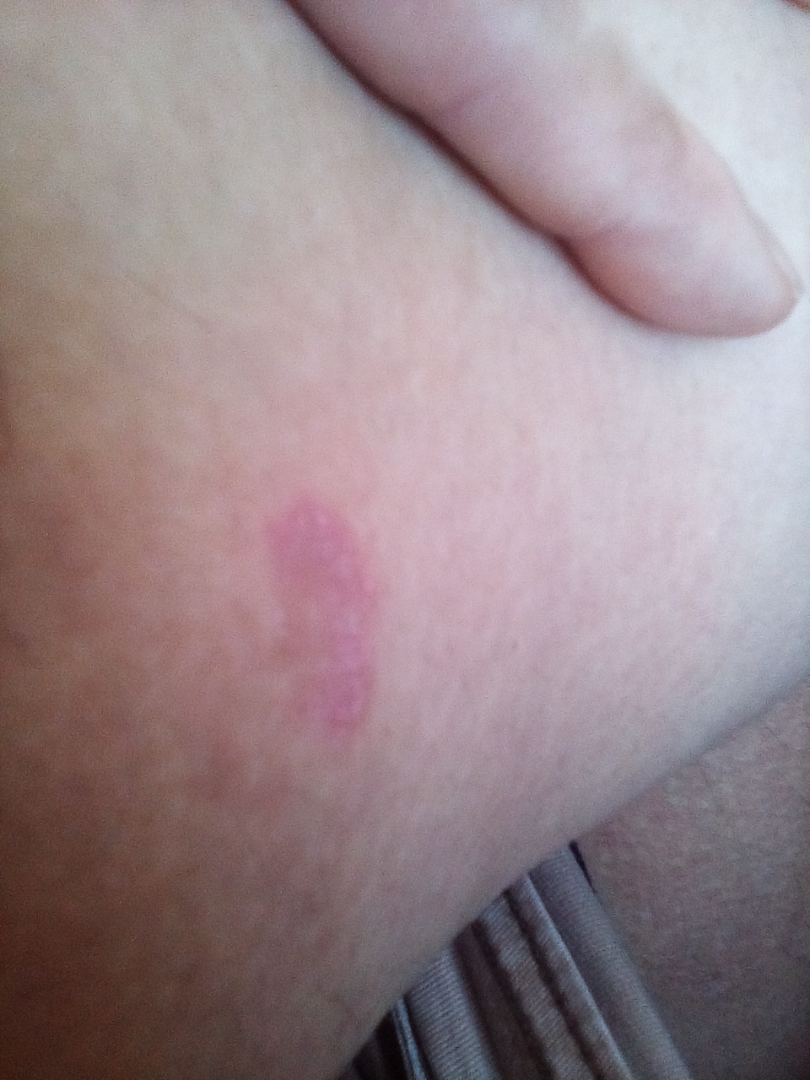Findings:
– image framing — at an angle
– subject — male, age 30–39
– body site — leg
– differential — Tinea and Eczema were each considered, in no particular order